A skin lesion imaged with a dermatoscope · a female patient roughly 35 years of age: 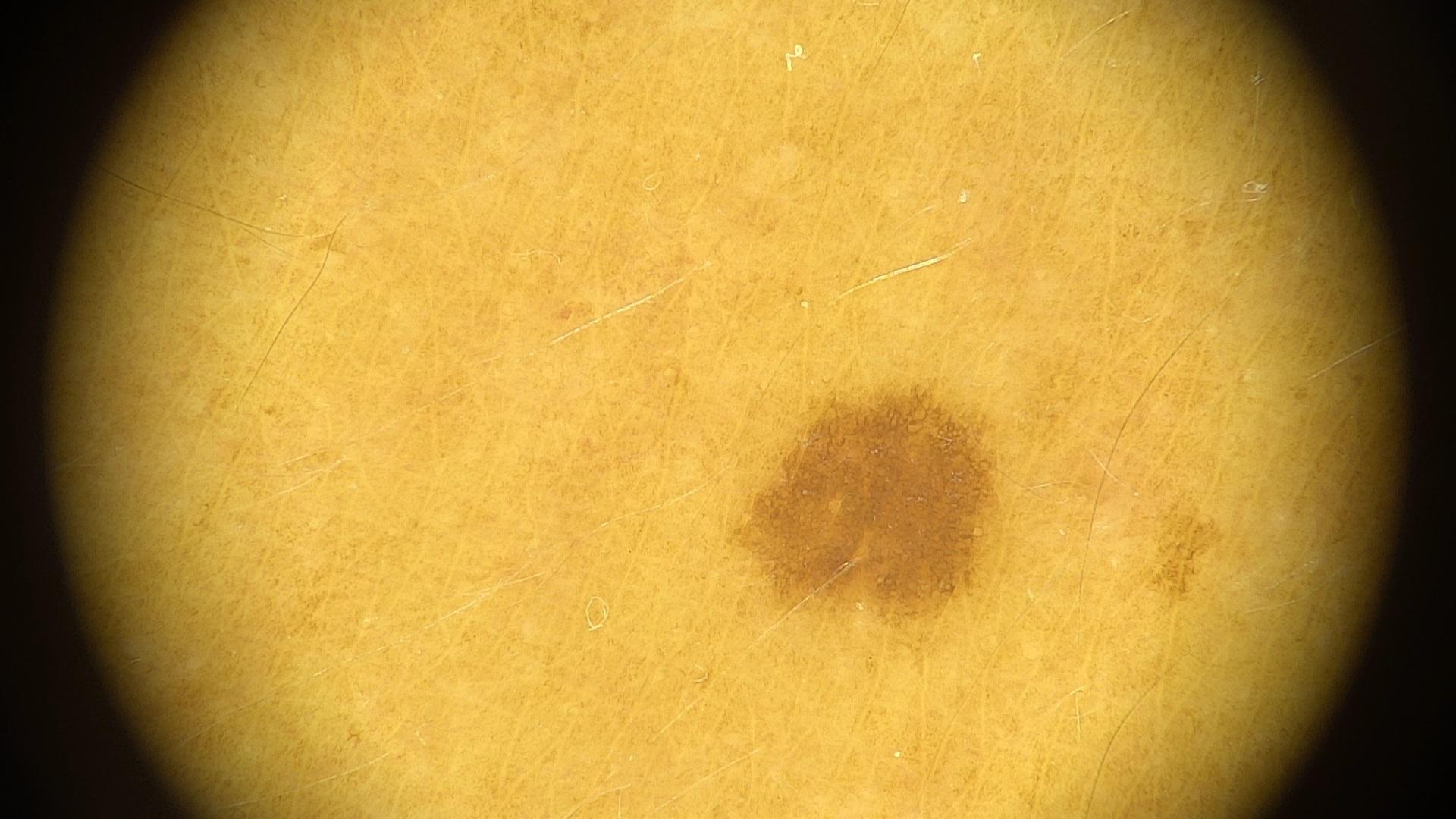The lesion involves an upper extremity. The clinical impression was a nevus.